The chart records prior skin cancer (patient or family) and prior malignancy (patient or family).
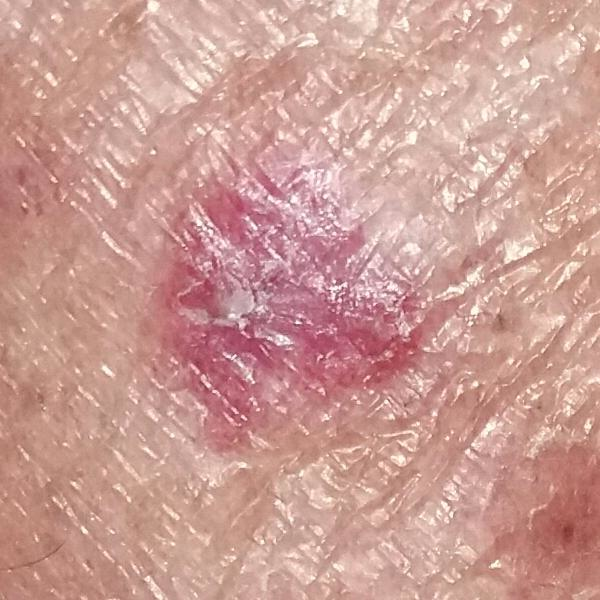The lesion is located on a thigh.
The lesion is roughly 10 by 9 mm.
Per patient report, the lesion itches.
Histopathology confirmed a malignant lesion — a squamous cell carcinoma.